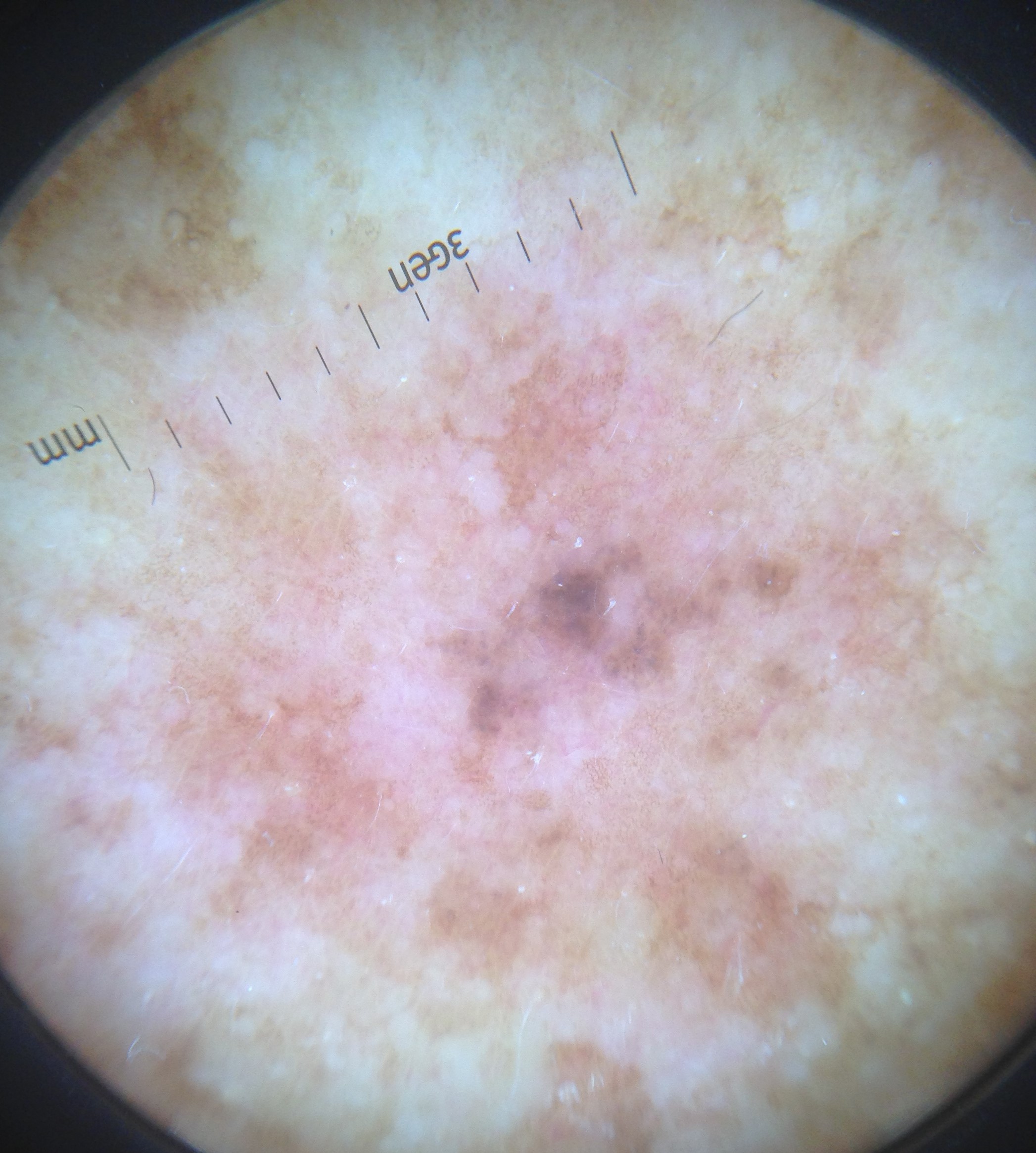A dermatoscopic image of a skin lesion. The morphology is that of a keratinocytic lesion. The diagnostic label was an actinic keratosis.